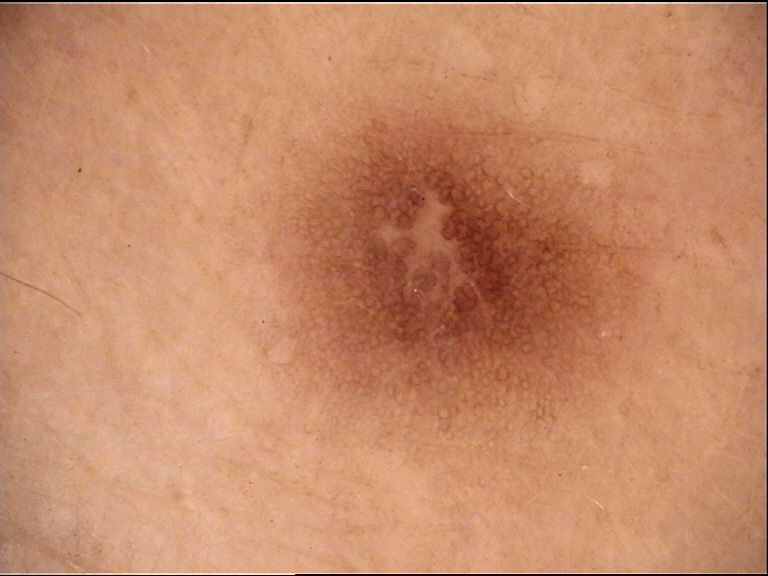imaging — dermatoscopy | classification — fibro-histiocytic | class — dermatofibroma (expert consensus).